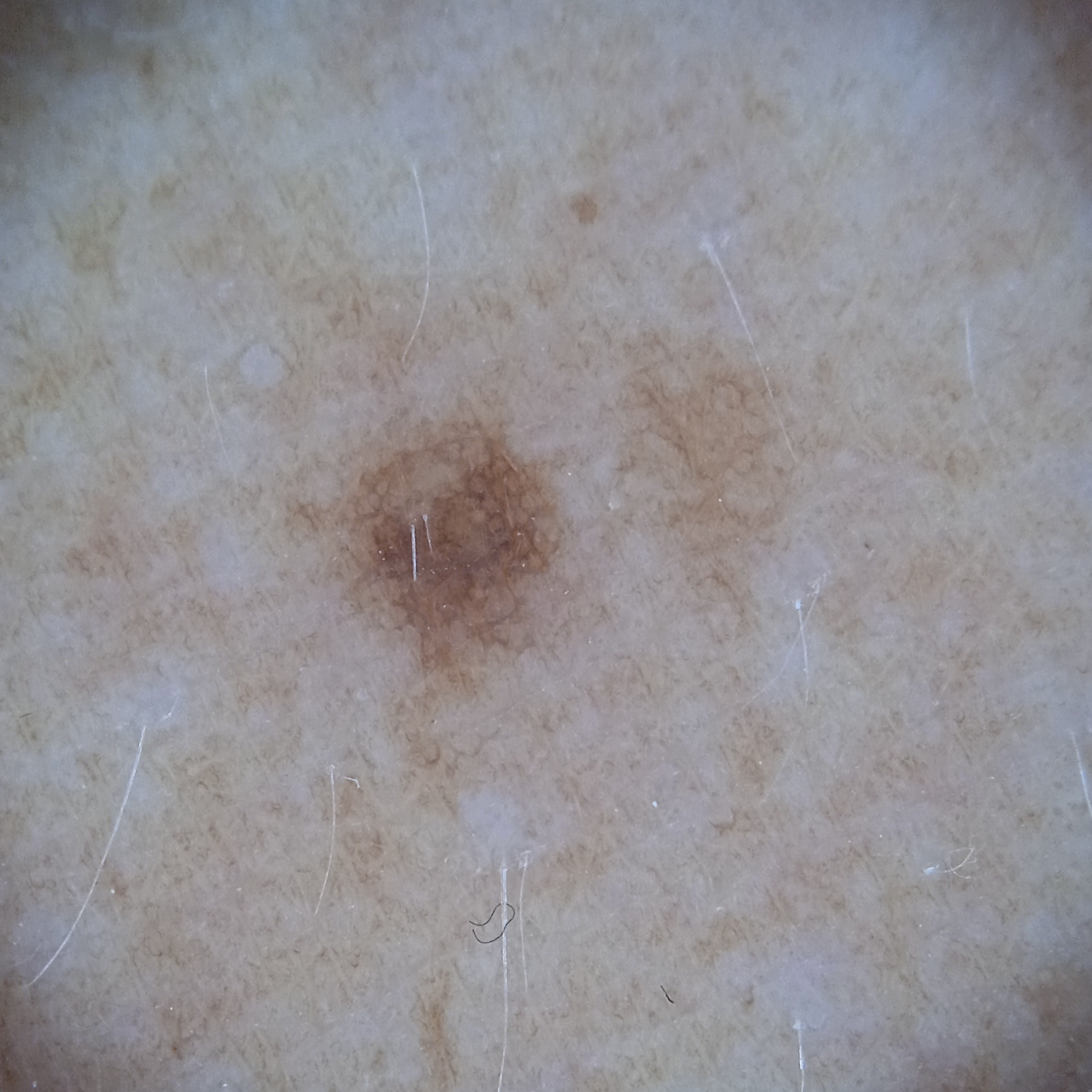The patient says their skin tans without first burning. A male subject 54 years old. By self-report, a personal history of cancer, no sunbed use, and no personal history of skin cancer. A moderate number of moles by the patient's own estimate. Acquired for a research image collection, with no referral diagnosis. Measuring roughly 2.9 mm. The dermatologists' assessment was a melanocytic nevus.